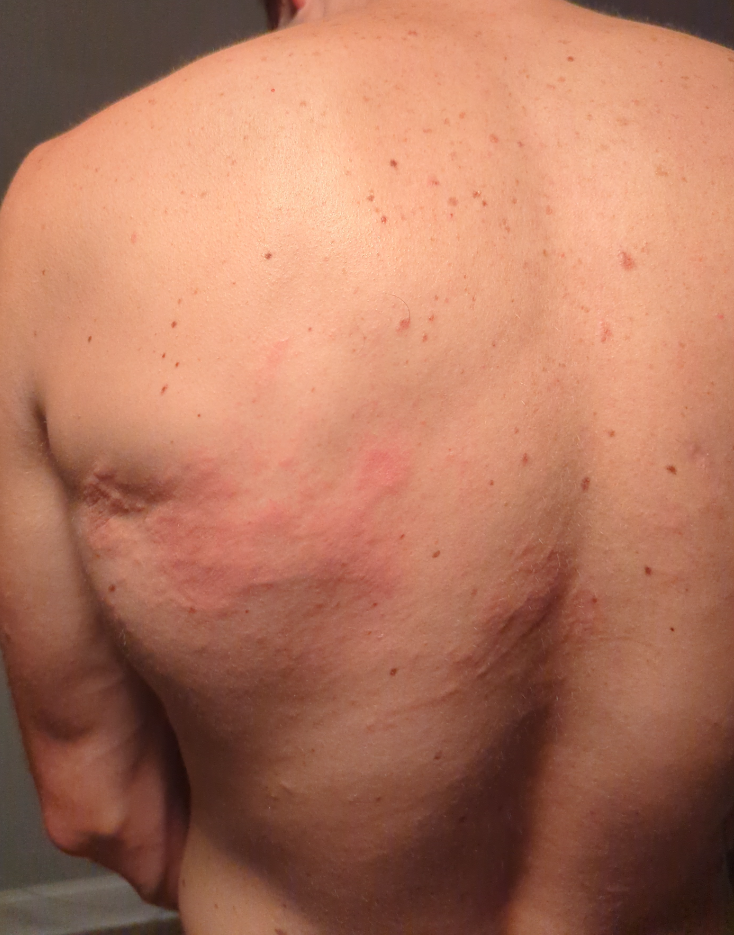Q: Who is the patient?
A: male, age 18–29
Q: What symptoms does the patient report?
A: enlargement and itching
Q: Duration?
A: one to four weeks
Q: What is the framing?
A: close-up
Q: How does the lesion feel?
A: raised or bumpy
Q: What is the patient's skin tone?
A: FST II; human graders estimated Monk Skin Tone 2 or 4
Q: Anatomic location?
A: back of the torso
Q: What conditions are considered?
A: the impression is Urticaria